A dermatoscopic image of a skin lesion: 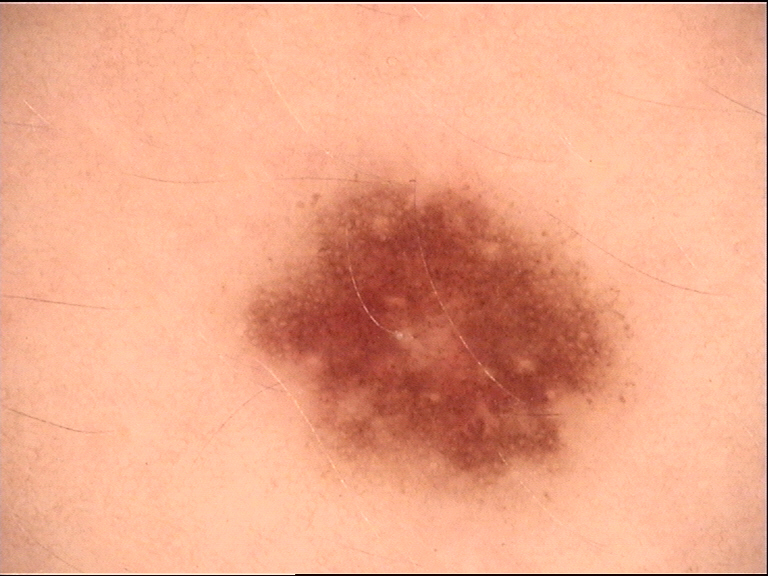Q: What was the diagnostic impression?
A: dysplastic junctional nevus (expert consensus)